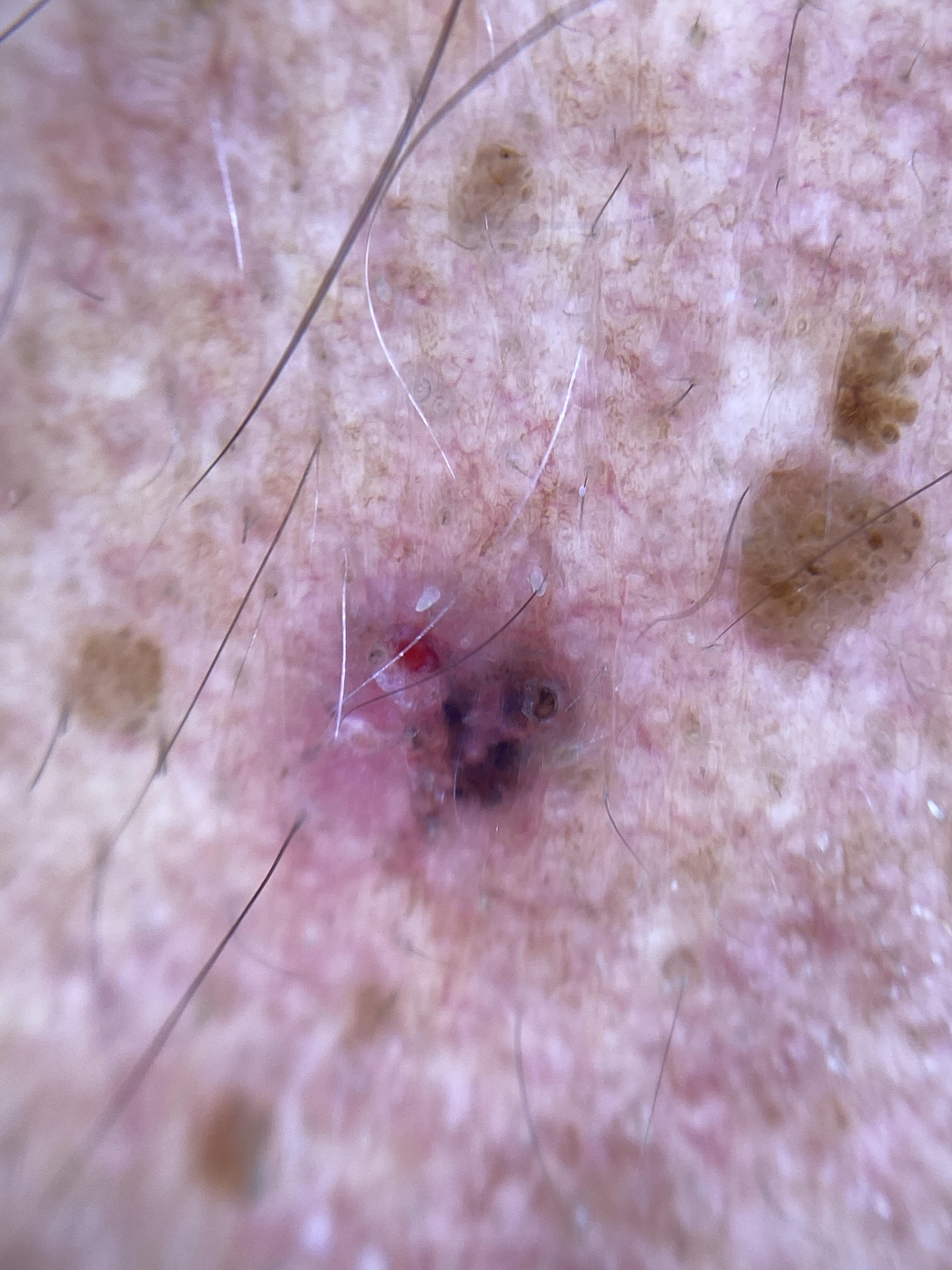Clinical context:
Dermoscopy of a skin lesion. FST III. Located on the head or neck.
Conclusion:
On biopsy, the diagnosis was a malignancy — a basal cell carcinoma.